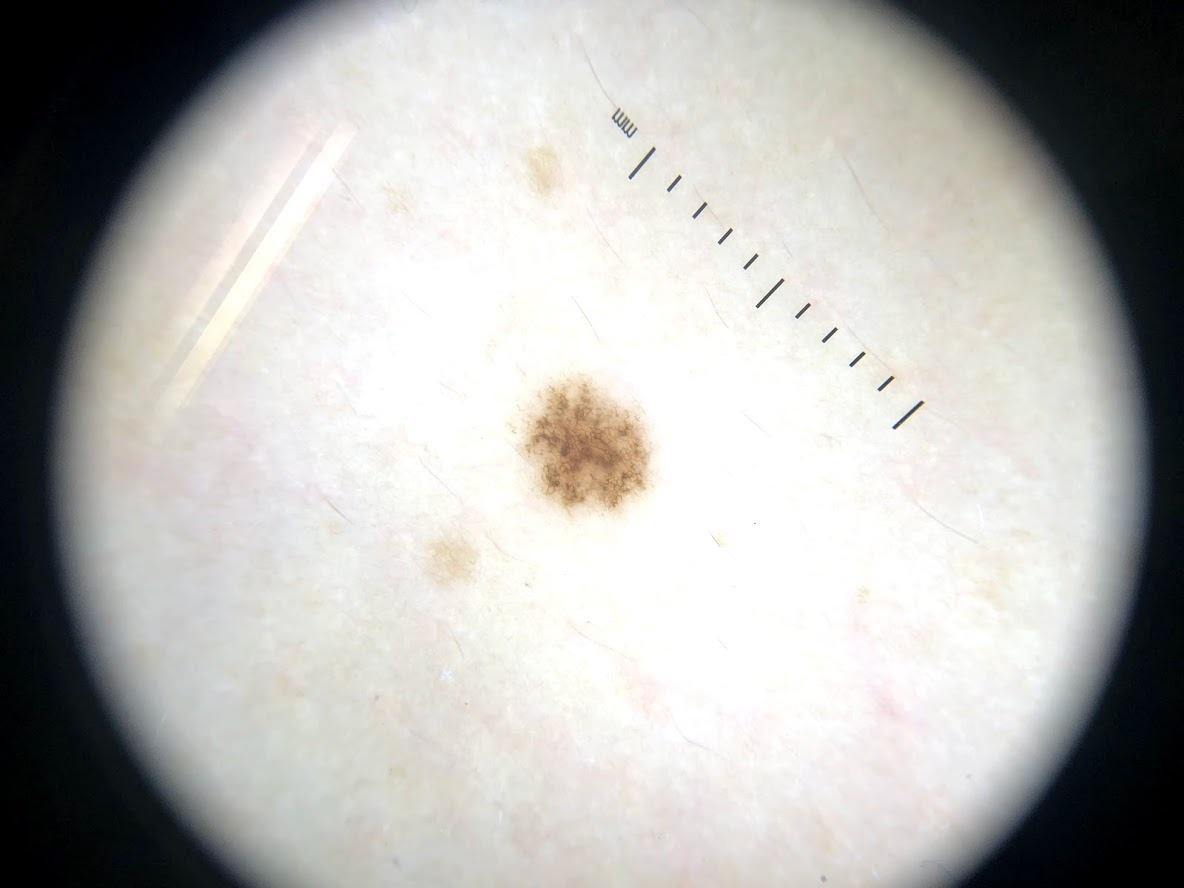modality = dermoscopy; patient = male, approximately 45 years of age; pathology = Nevus (biopsy-proven).